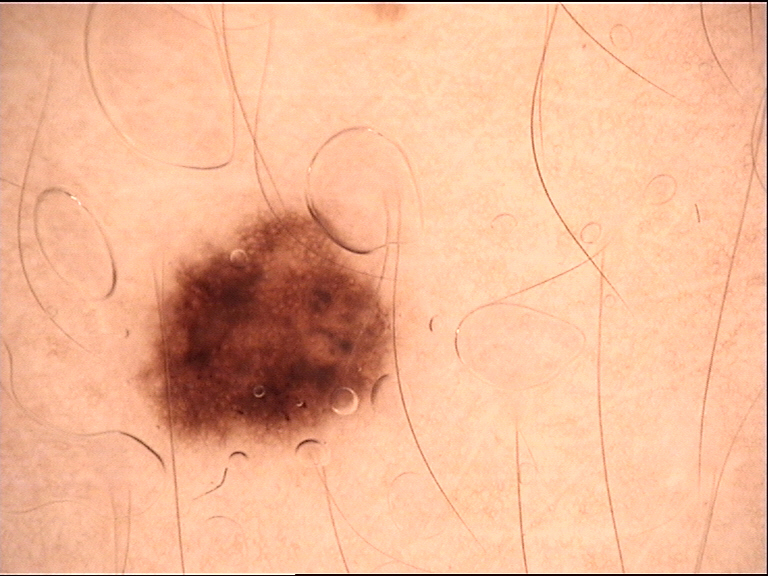Dermoscopy of a skin lesion. The diagnostic label was a benign lesion — a dysplastic junctional nevus.